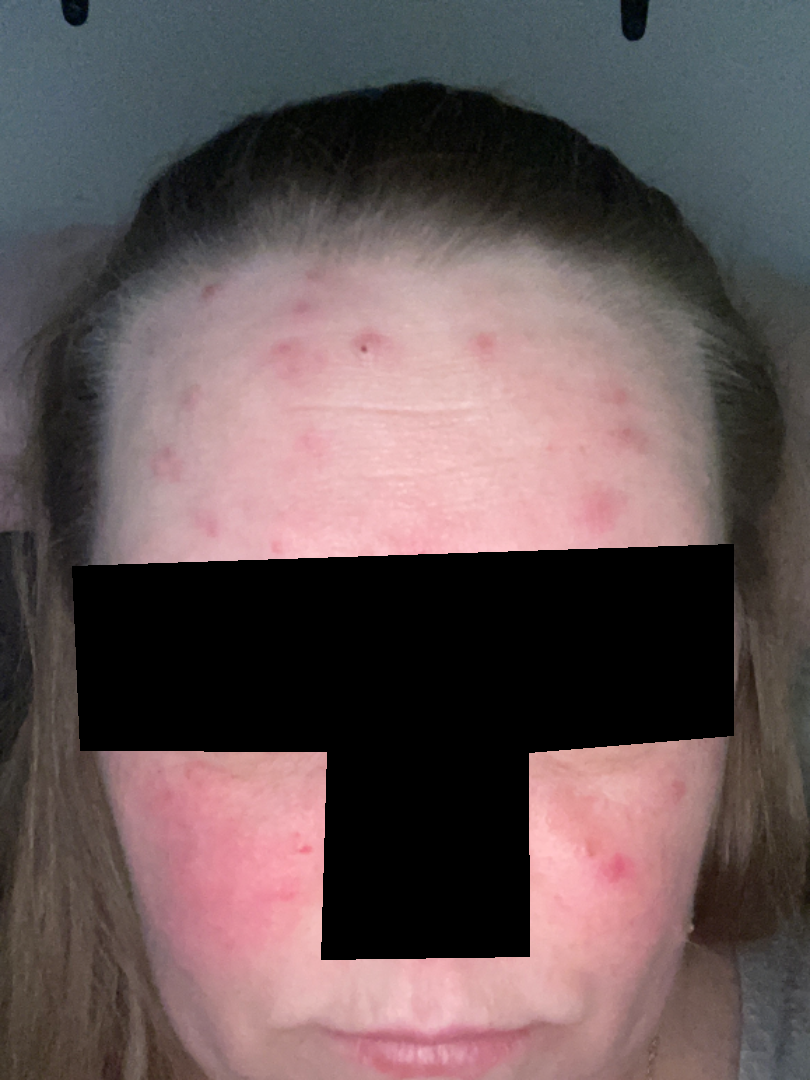| key | value |
|---|---|
| differential diagnosis | most consistent with Rosacea |